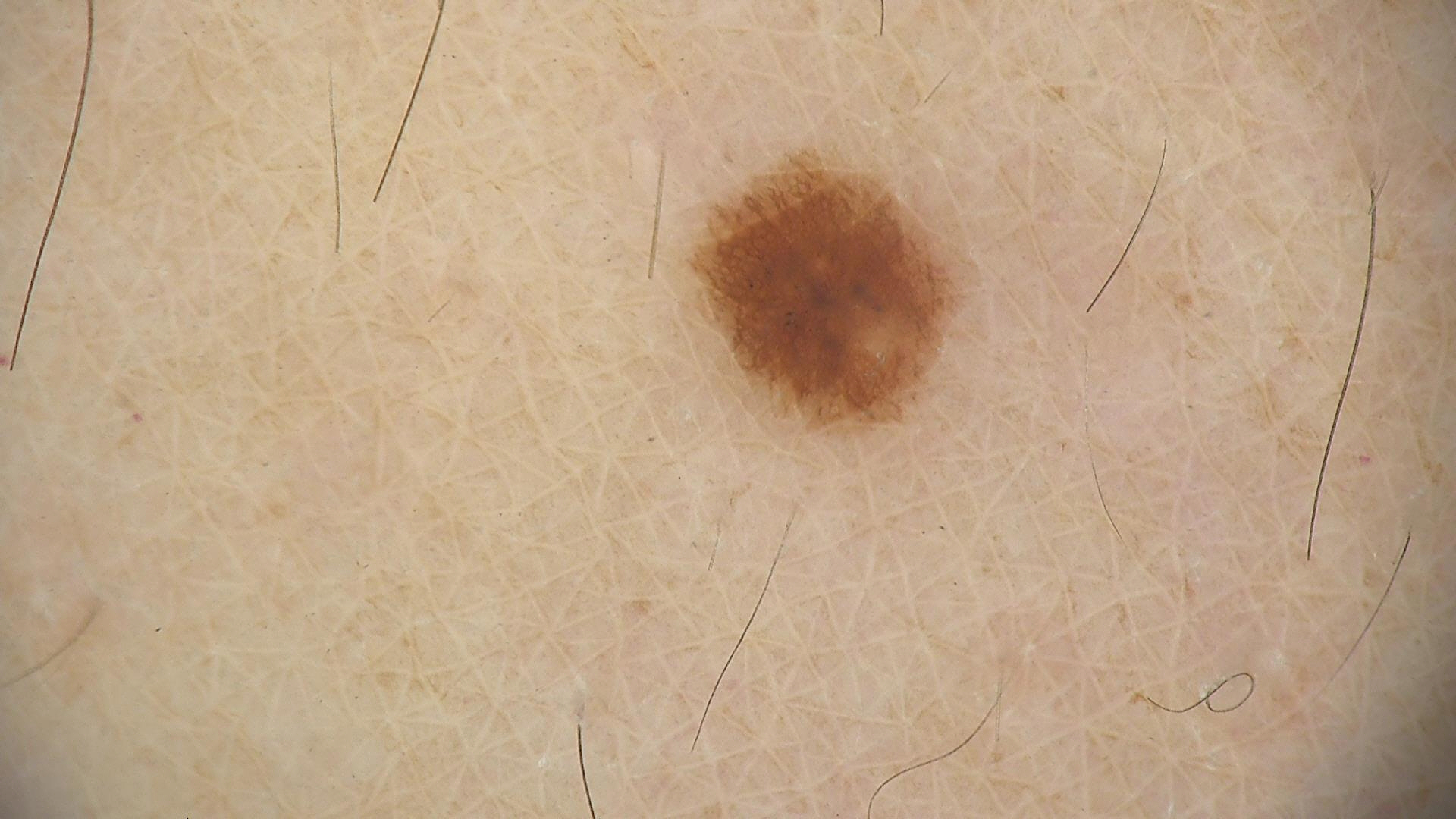Summary:
A dermoscopic close-up of a skin lesion.
Impression:
Labeled as a dysplastic junctional nevus.